This is a close-up image · female subject, age 18–29:
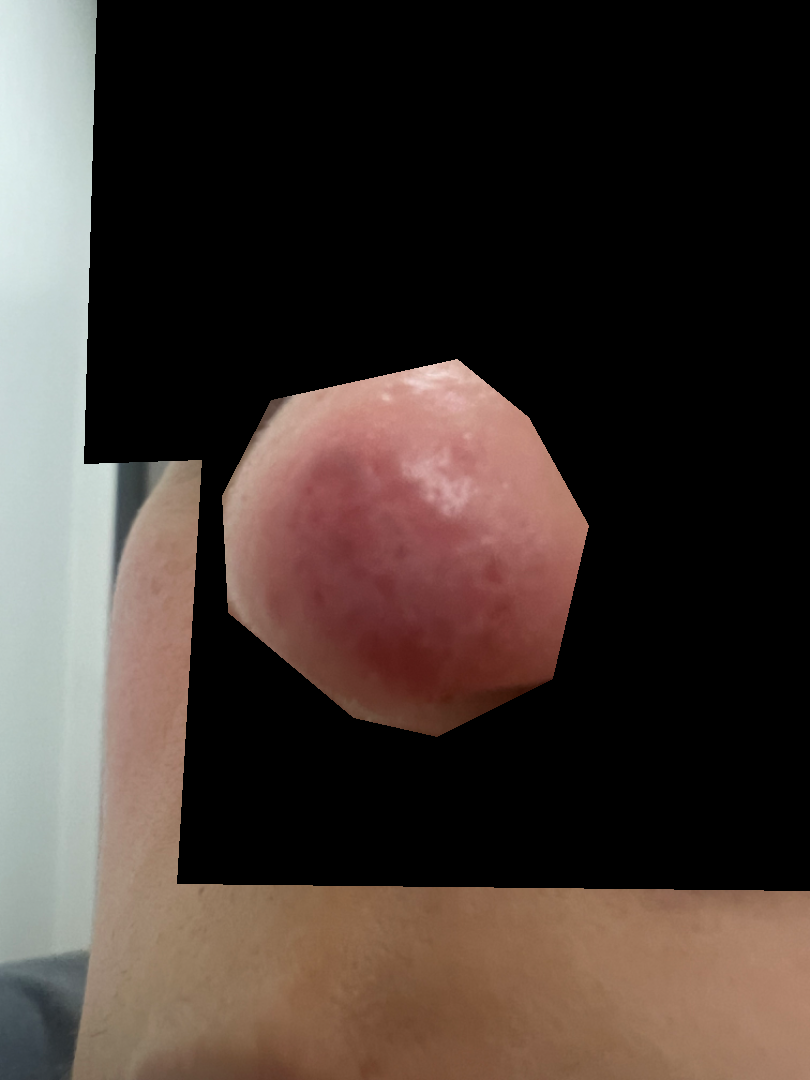The skin condition could not be confidently assessed from this image.